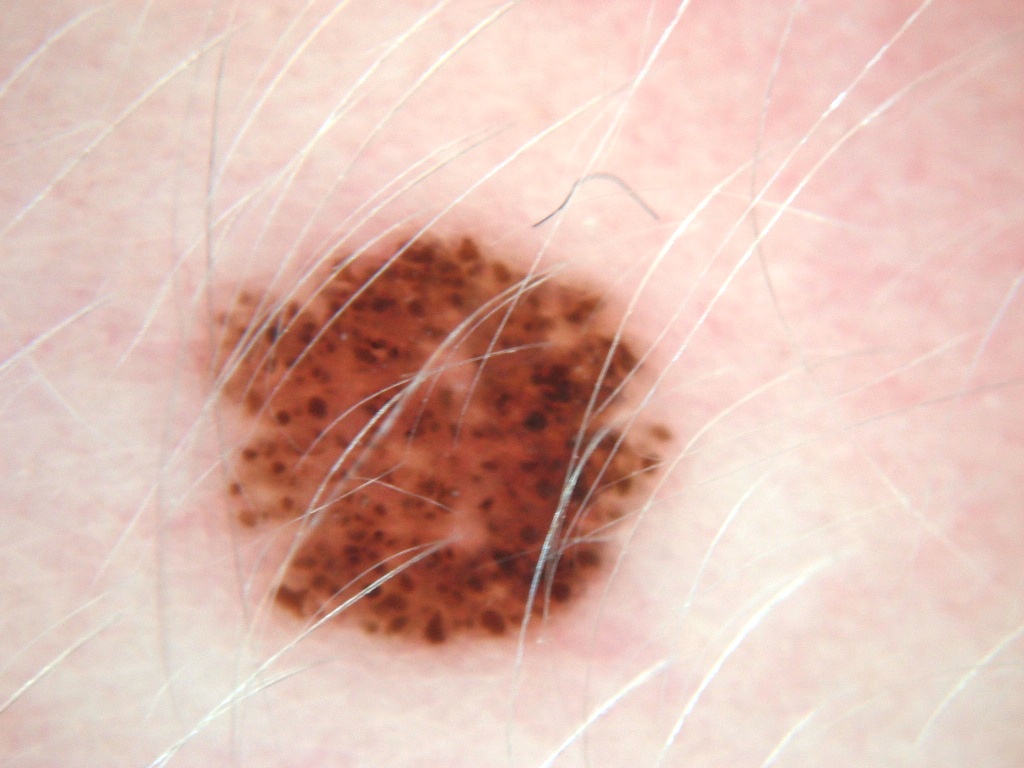A dermoscopic image of a skin lesion. The subject is a male aged 8 to 12. The lesion takes up about 22% of the image. Dermoscopic examination shows globules; no milia-like cysts, negative network, pigment network, or streaks. The visible lesion spans [186, 218, 687, 663]. The lesion was assessed as a melanocytic nevus, a benign lesion.